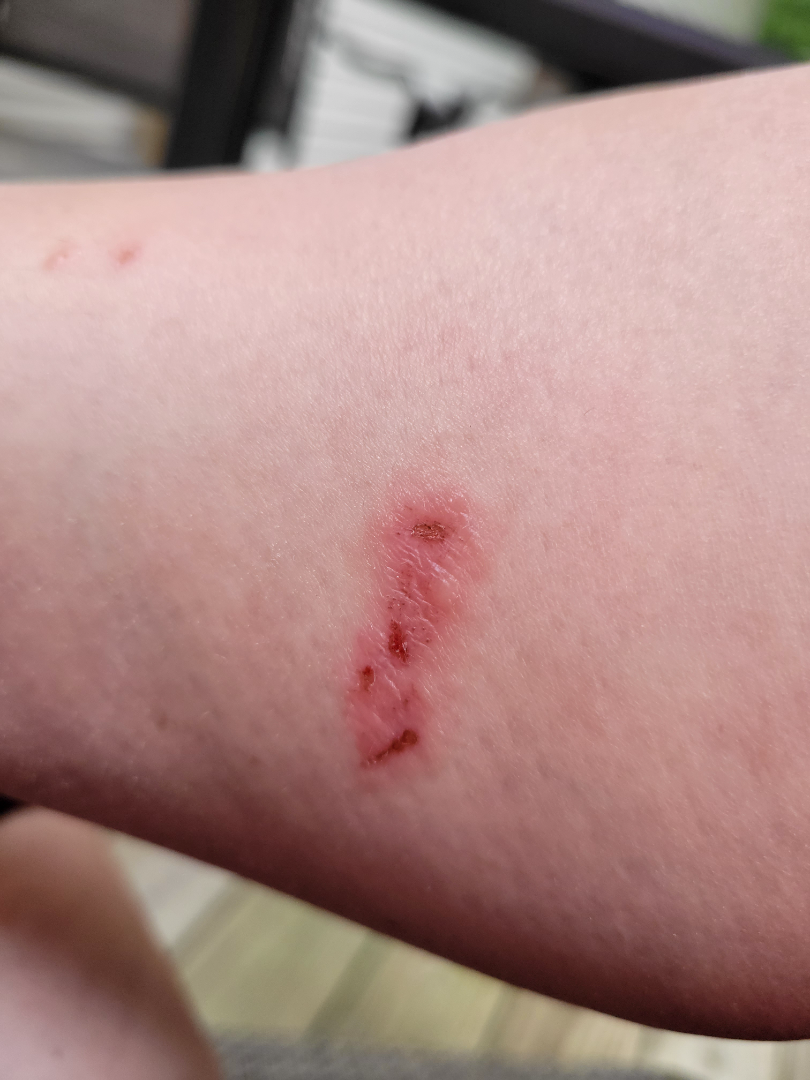| field | value |
|---|---|
| assessment | not assessable |